A patient in their 70s · a smartphone photograph of a skin lesion — 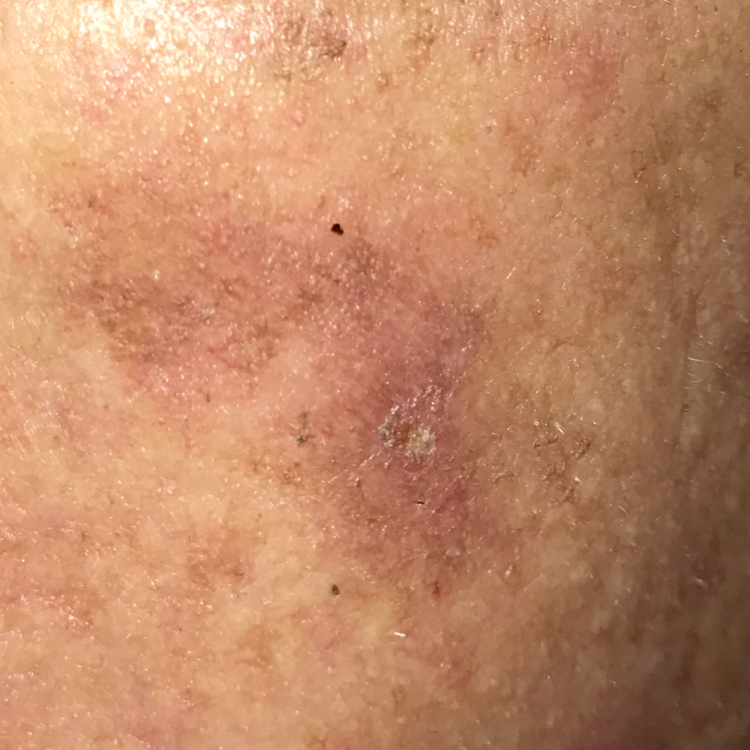body site: the face; patient-reported symptoms: itching / no bleeding, no growth; diagnosis: actinic keratosis (clinical consensus).